The photo was captured at a distance. The lesion involves the arm and leg. The subject is 18–29, female. No constitutional symptoms were reported. The lesion is described as rough or flaky and raised or bumpy. Symptoms reported: enlargement, bothersome appearance, burning, darkening, bleeding and itching.
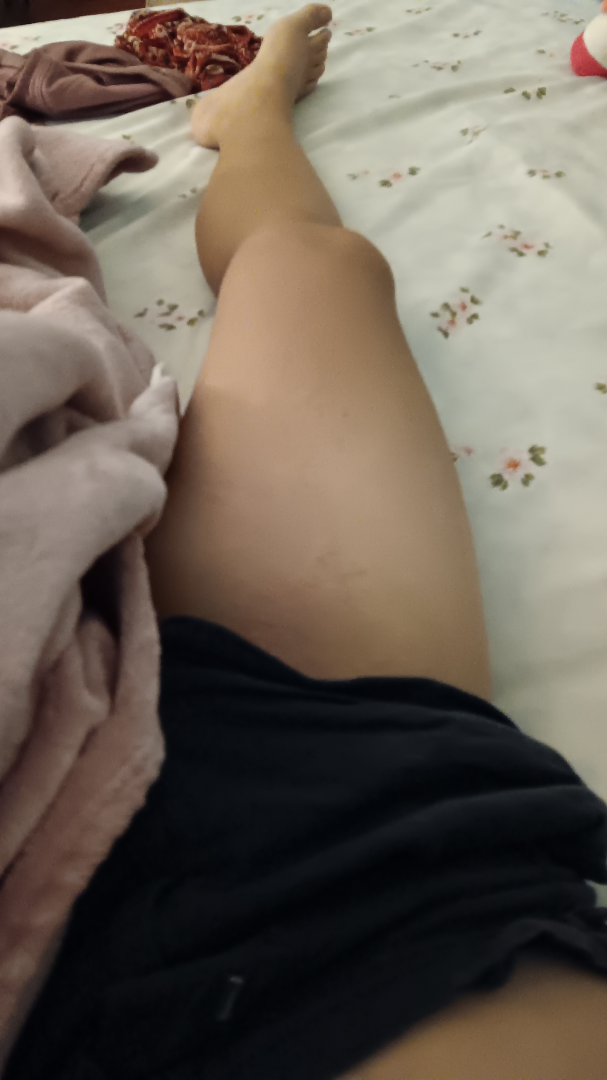  differential:
    leading:
      - Eczema
    considered:
      - Urticaria
      - Allergic Contact Dermatitis